A dermoscopic image of a skin lesion · the patient says their skin tans without first burning · the patient describes having few moles overall · on a questionnaire the patient reported a personal history of skin cancer · acquired for a research image collection, with no referral diagnosis.
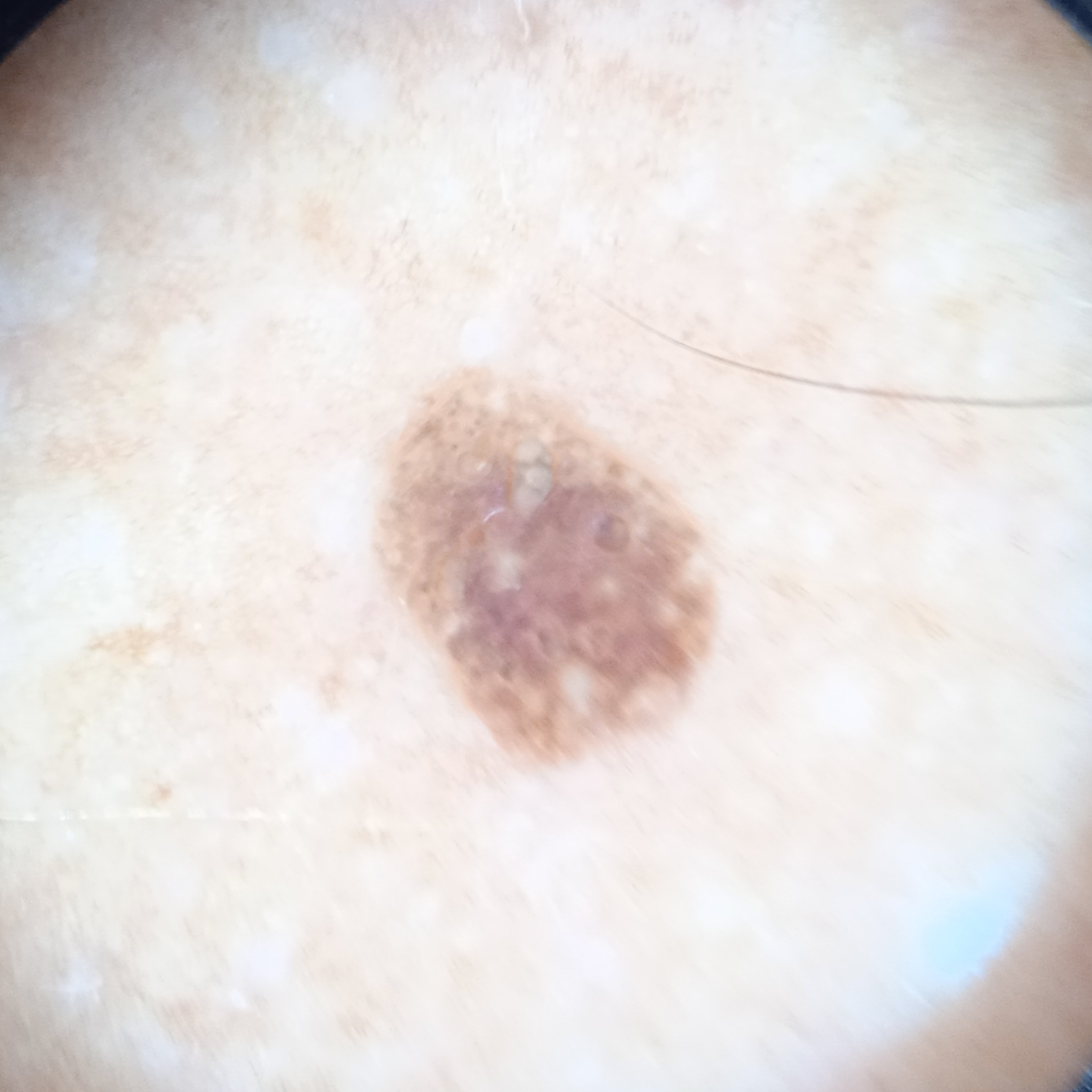| field | value |
|---|---|
| diameter | 5.2 mm |
| diagnosis | seborrheic keratosis (dermatologist consensus) |